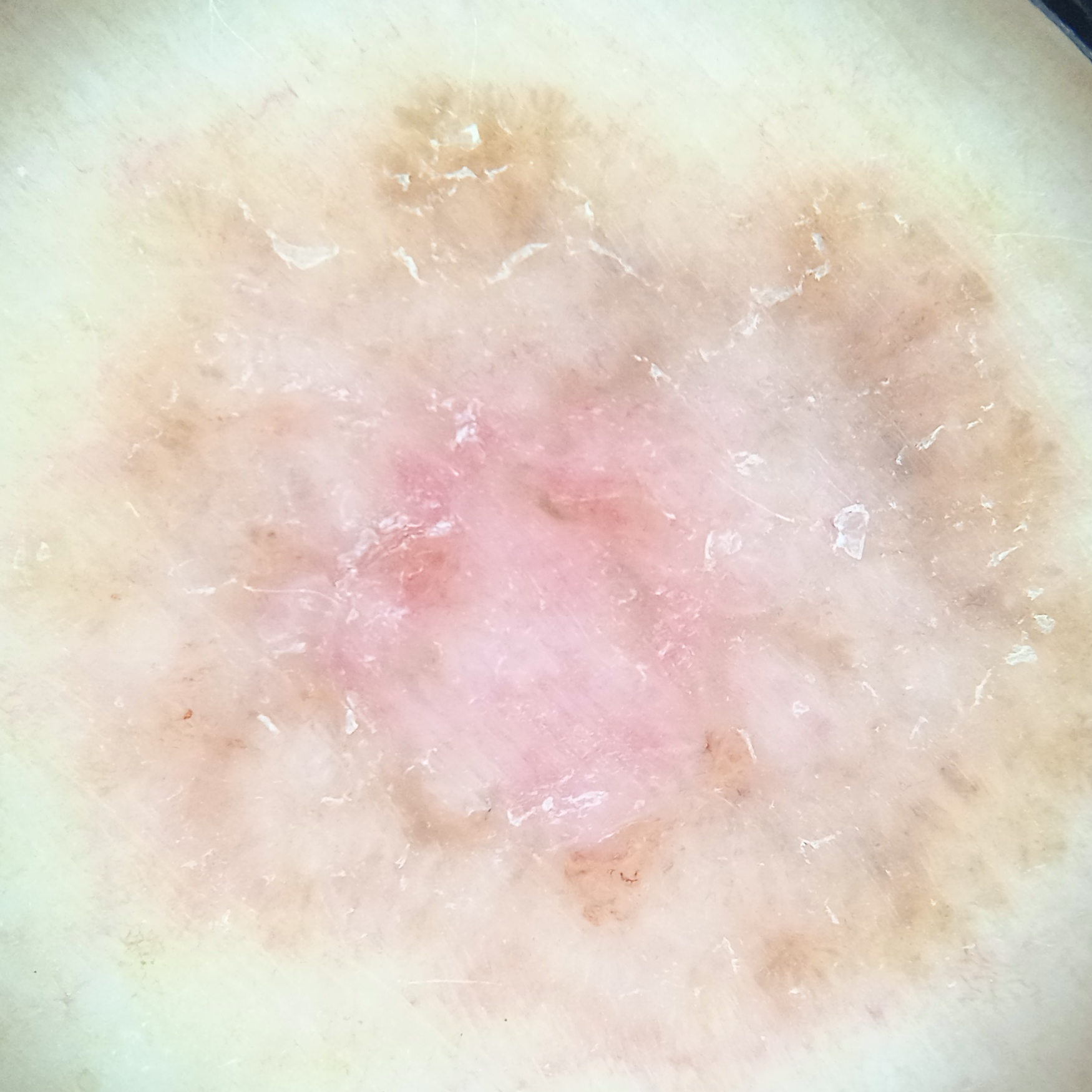Referred with a clinical suspicion of basal cell carcinoma.
A dermatoscopic image of a skin lesion.
A female subject age 60.
The lesion was assessed as a basal cell carcinoma.